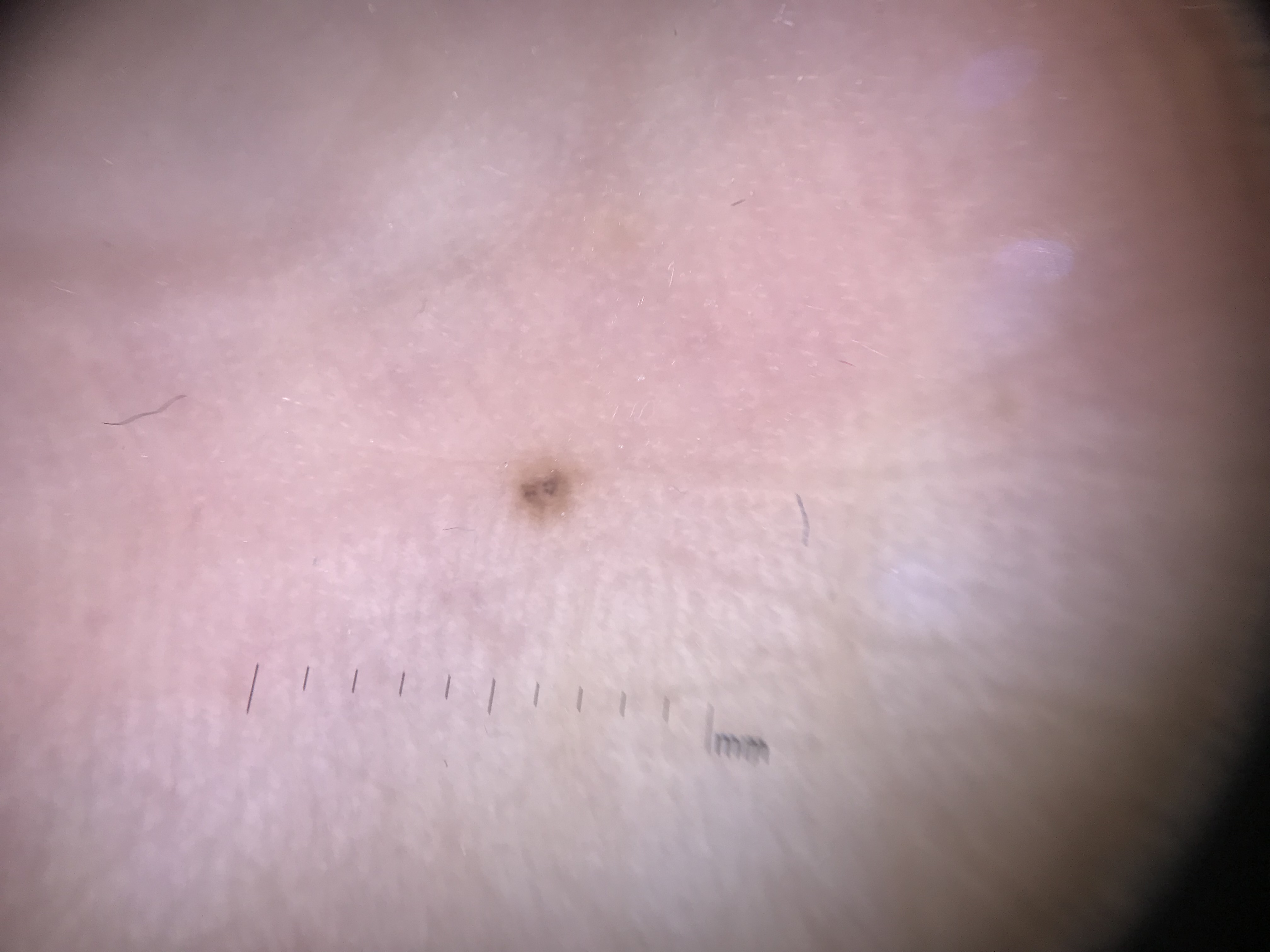diagnosis:
  name: acral junctional nevus
  code: ajb
  malignancy: benign
  super_class: melanocytic
  confirmation: expert consensus